Per the chart, a prior melanoma; the patient was assessed as Fitzpatrick phototype II; a female patient roughly 65 years of age: 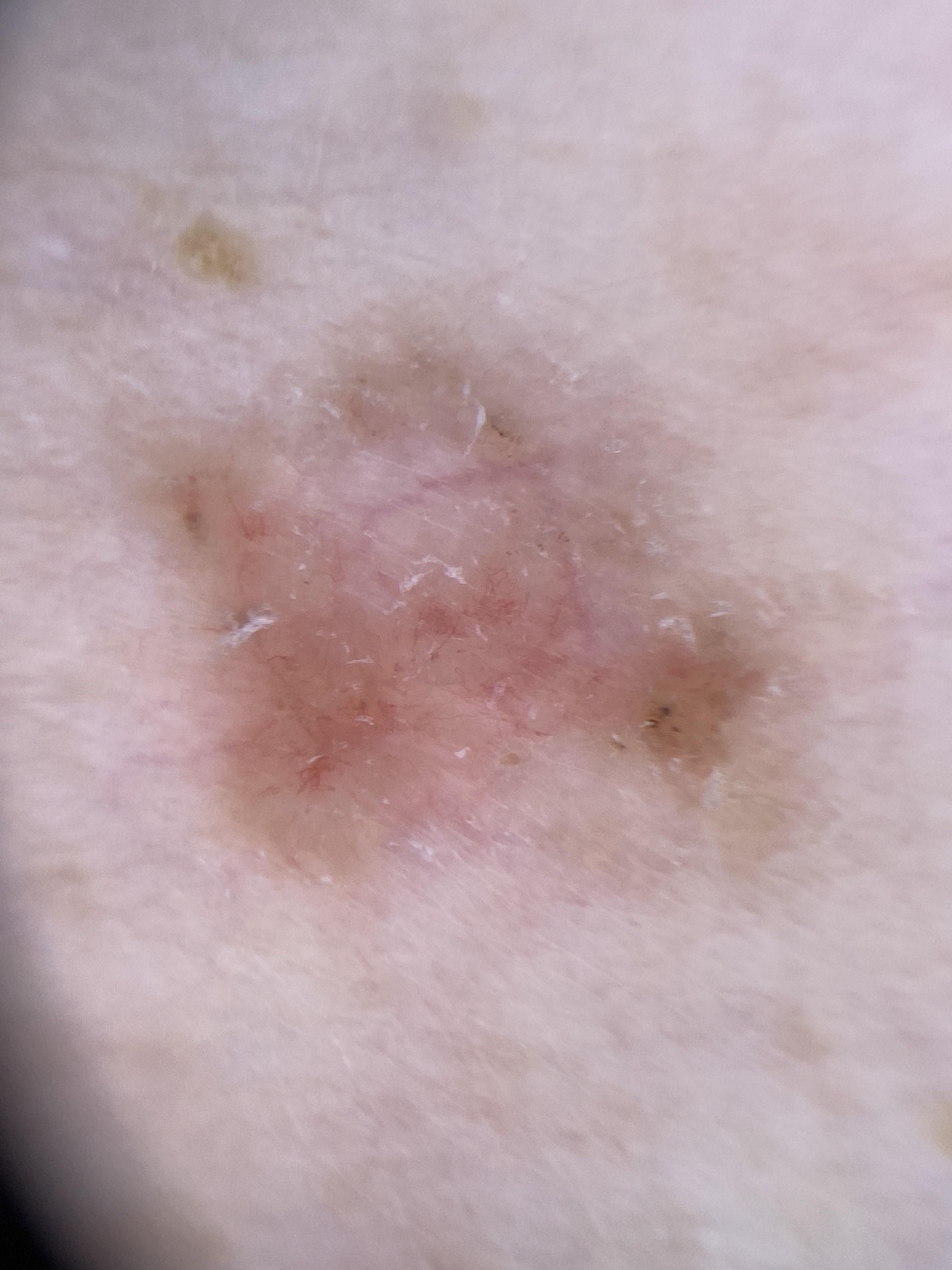anatomic site=the trunk | diagnosis=Basal cell carcinoma (biopsy-proven).